Contact-polarized dermoscopy of a skin lesion — 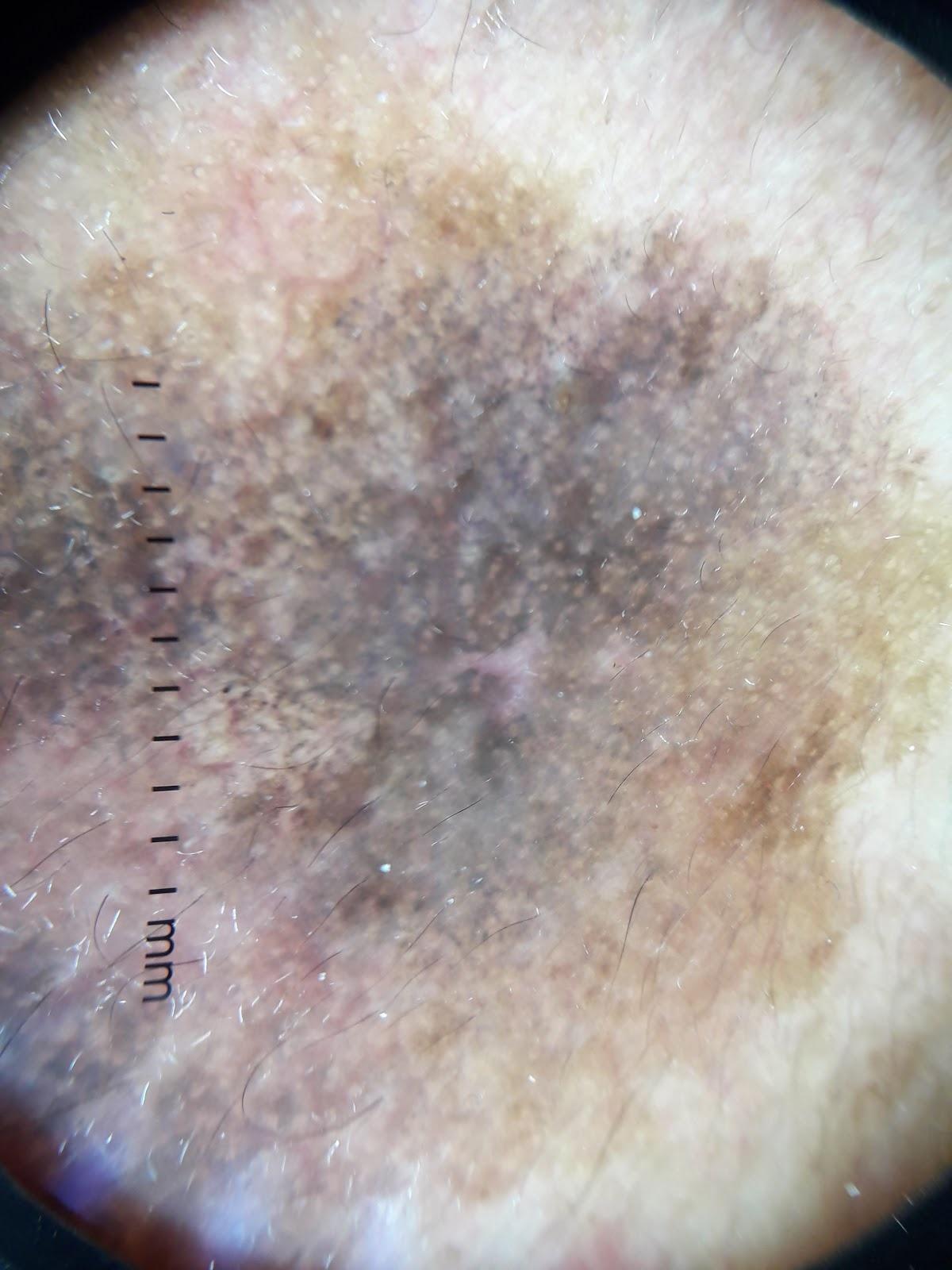Located on the head or neck. Histopathological examination showed a melanoma.